Fitzpatrick skin type III; a male subject aged approximately 40; the chart records melanoma in a first-degree relative but no previous melanoma; a dermatoscopic image of a skin lesion — 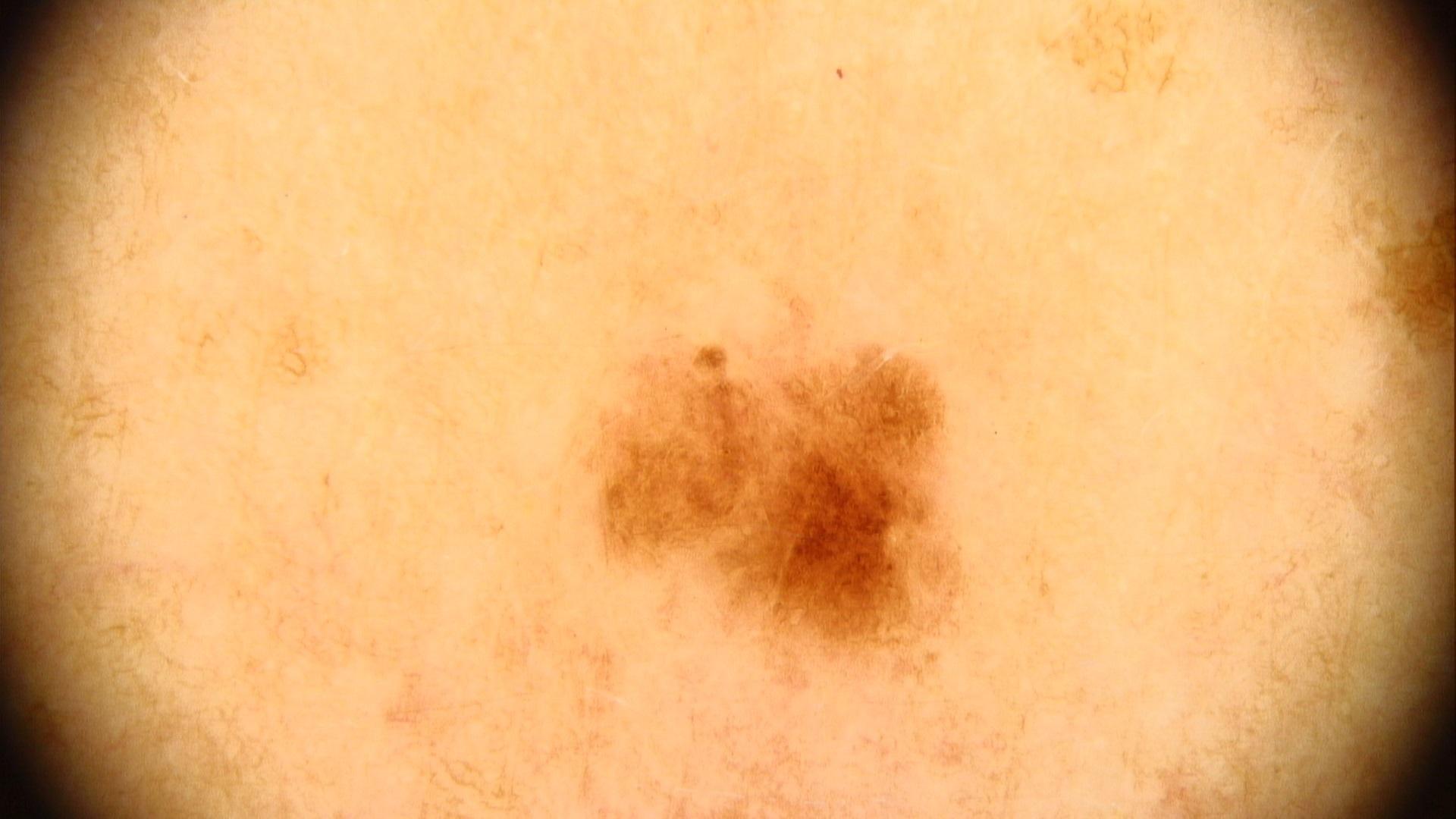diagnosis=Nevus (clinical impression).